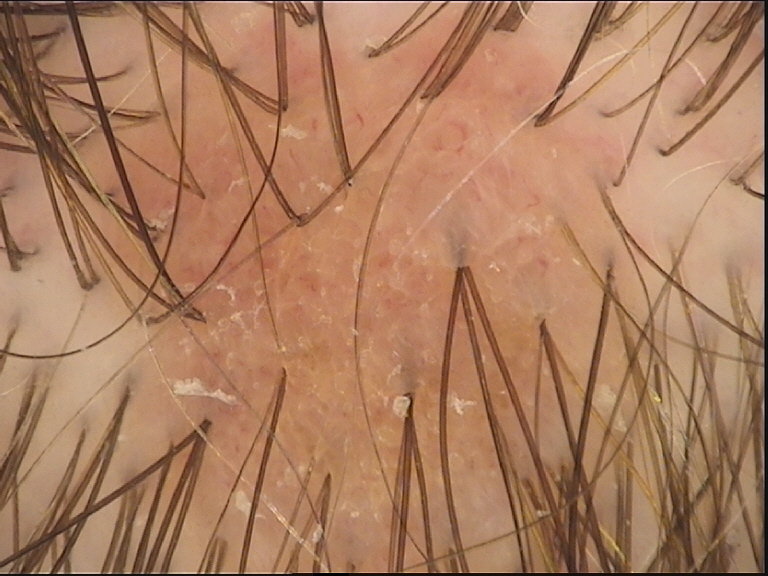Diagnosed as a keratinocytic, benign lesion — a seborrheic keratosis.